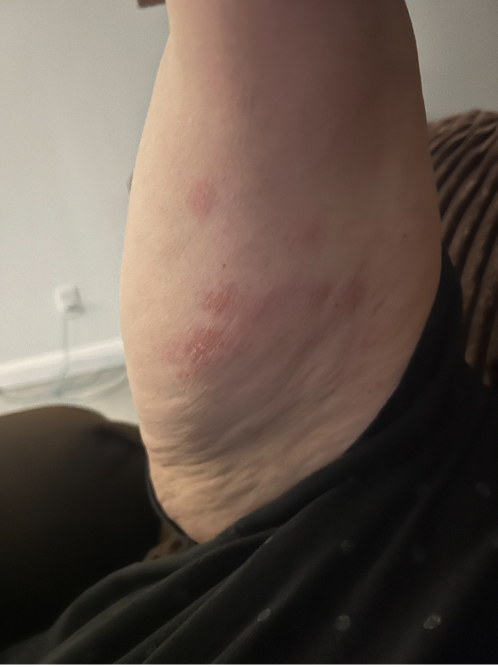surface texture: flat, raised or bumpy and rough or flaky; site: arm and leg; patient describes the issue as: skin that appeared healthy to them; shot type: at an angle; associated systemic symptoms: fatigue and joint pain; diagnostic considerations: the differential is split between Cutaneous T Cell Lymphoma, Granuloma annulare and Eczema.